The patient was assessed as skin type III; dermoscopy of a skin lesion; the chart documents a first-degree relative with melanoma but no prior melanoma; a female subject in their mid- to late 30s: 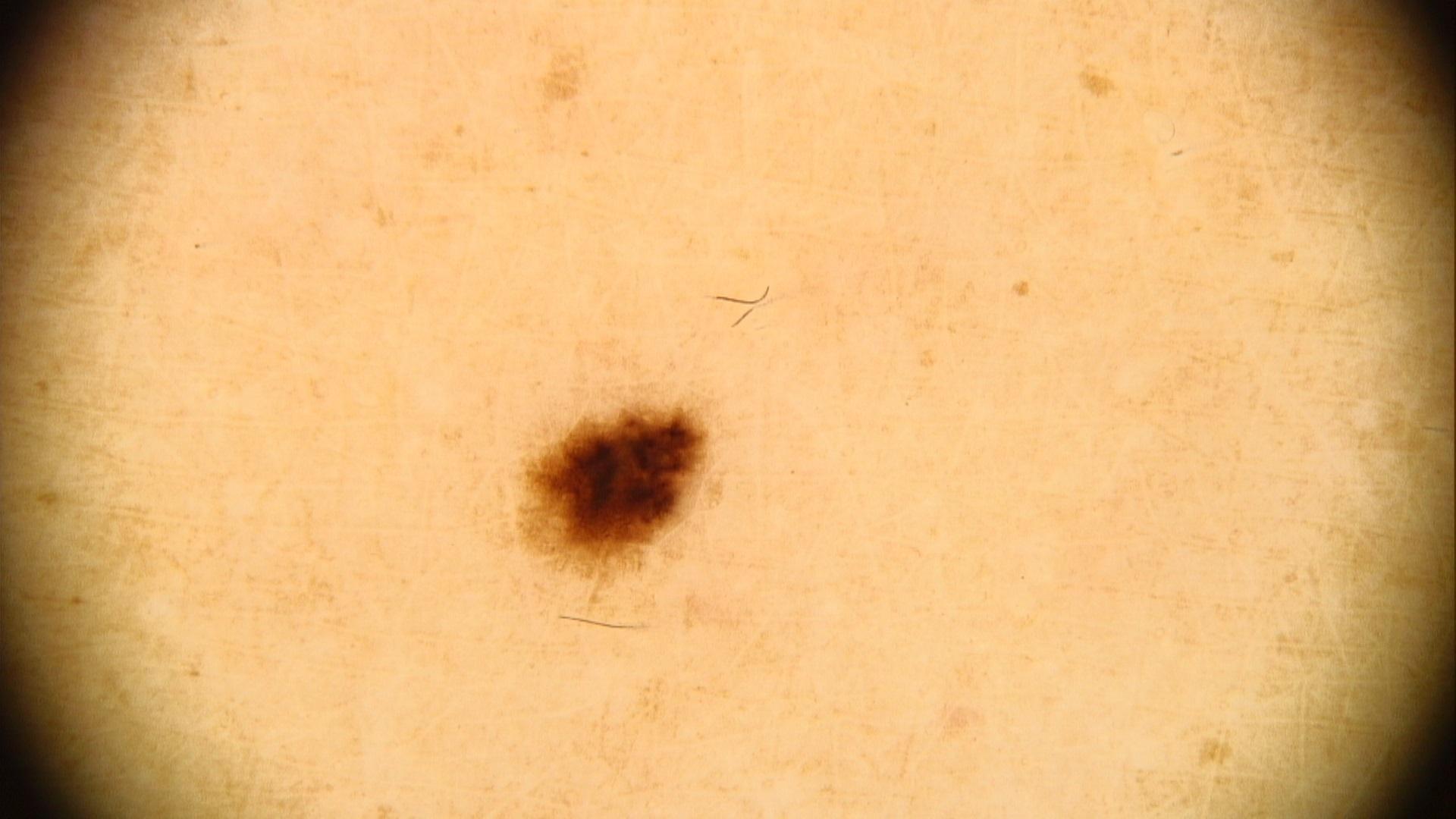Case summary:
The lesion is on a lower extremity.
Assessment:
The diagnostic impression was a nevus.